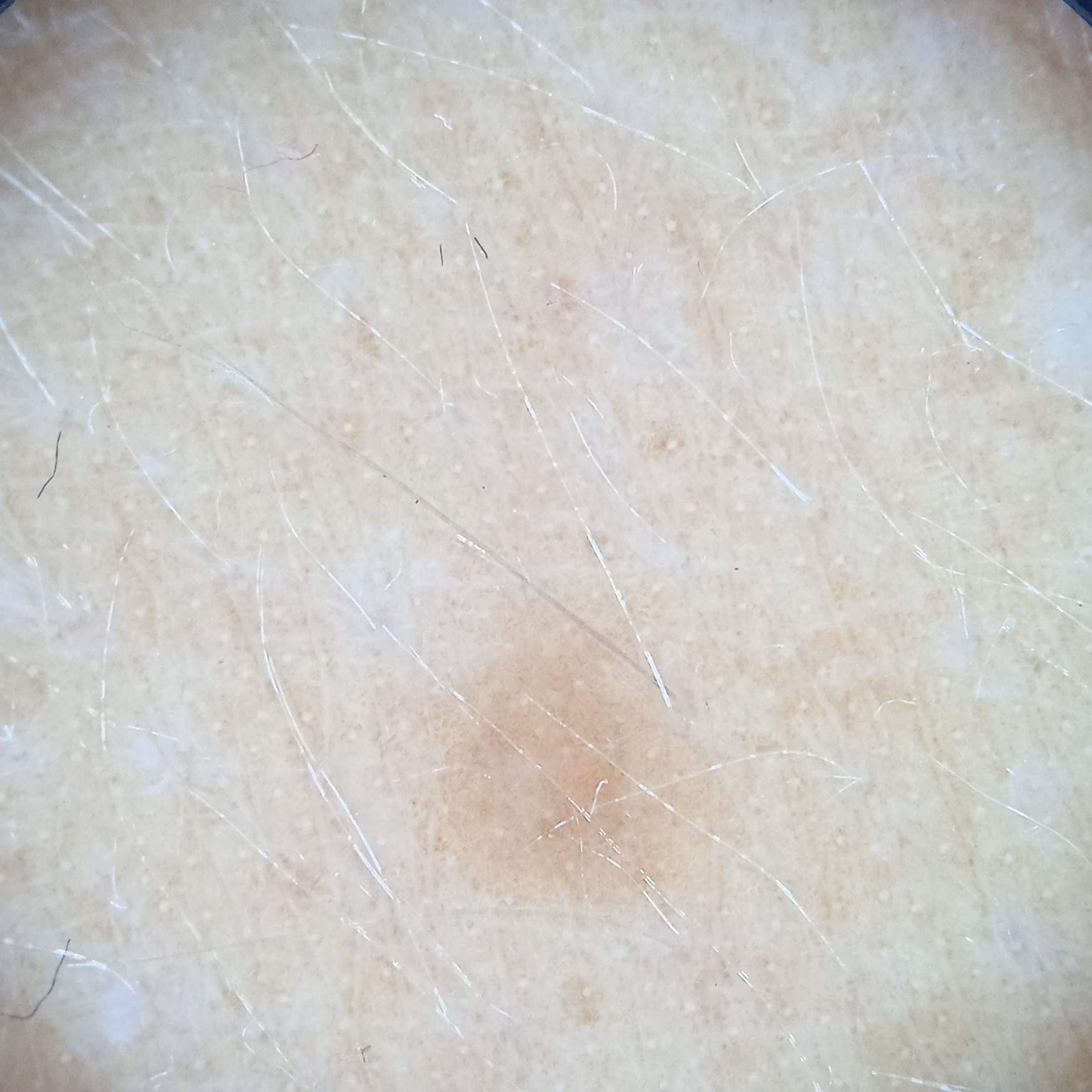The reviewing dermatologists could not reach a confident diagnosis. | field | value |
|---|---|
| referral | research study (no referral diagnosis) |
| image type | dermoscopic image |
| sun reaction | skin tans without first burning |
| relevant history | a history of sunbed use |
| nevus count | a moderate number of melanocytic nevi |
| subject | female, age 47 |
| location | the back |
| diameter | 3.5 mm |